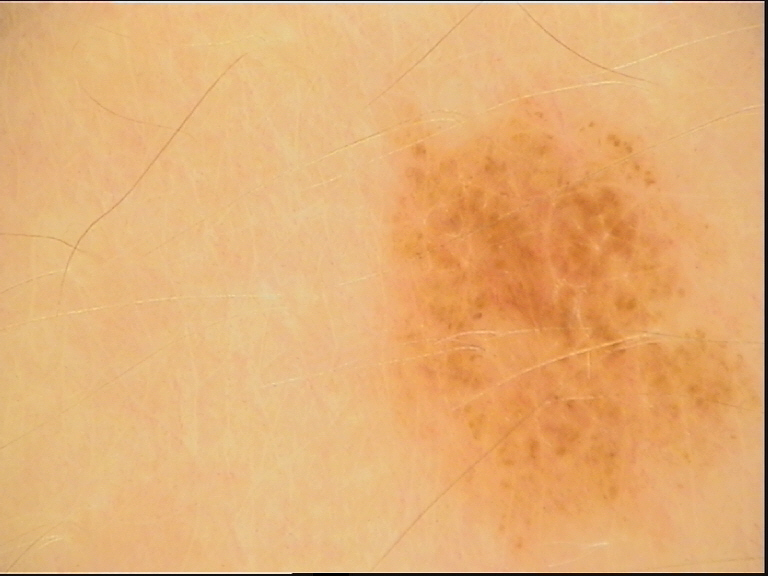Q: What kind of image is this?
A: dermoscopy
Q: What was the diagnostic impression?
A: dysplastic junctional nevus (expert consensus)